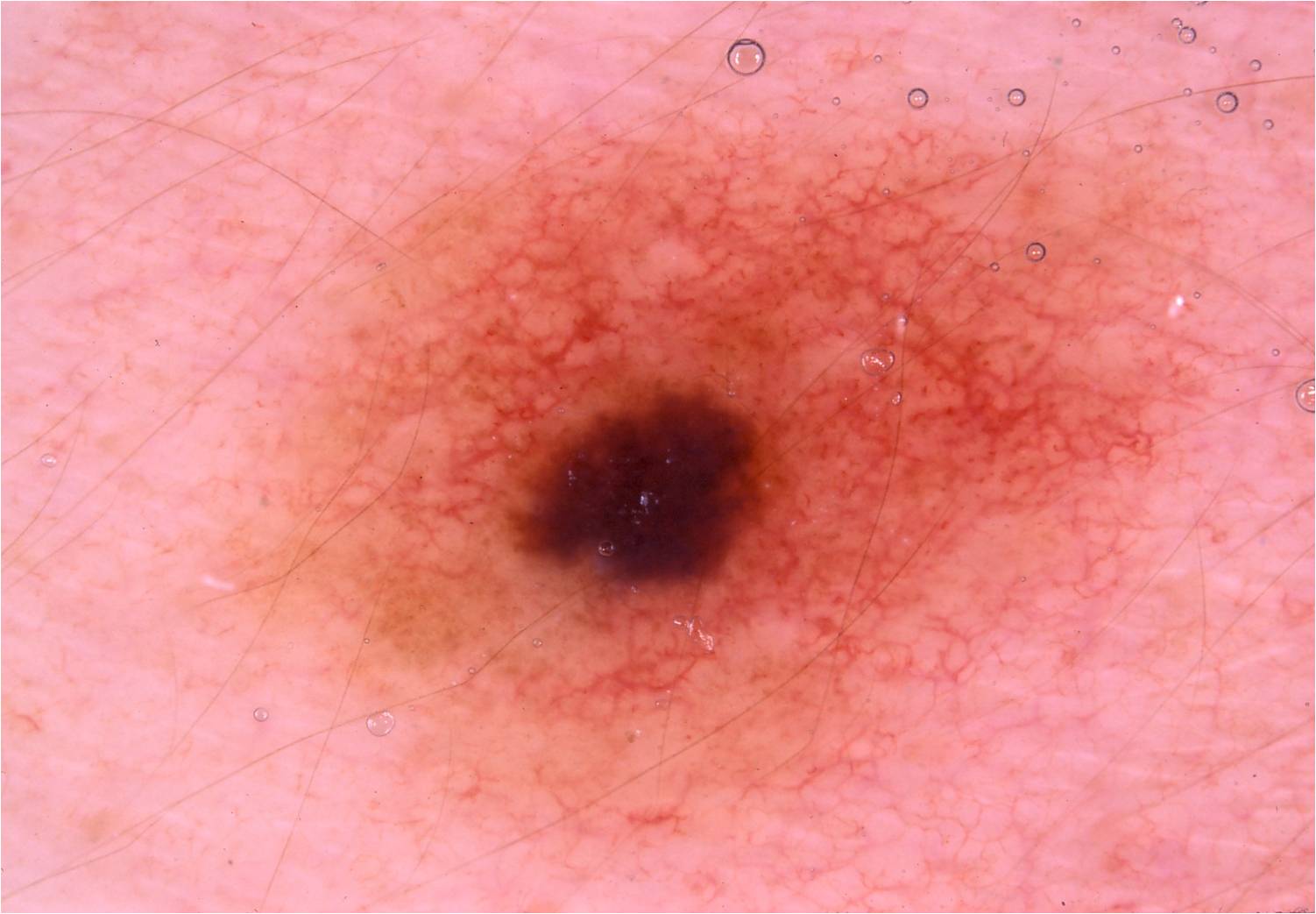imaging = dermoscopy
subject = male, aged 33-37
dermoscopic features assessed but absent = negative network, streaks, globules, milia-like cysts, and pigment network
extent = large
location = 229/109/1216/841
assessment = a melanocytic nevus